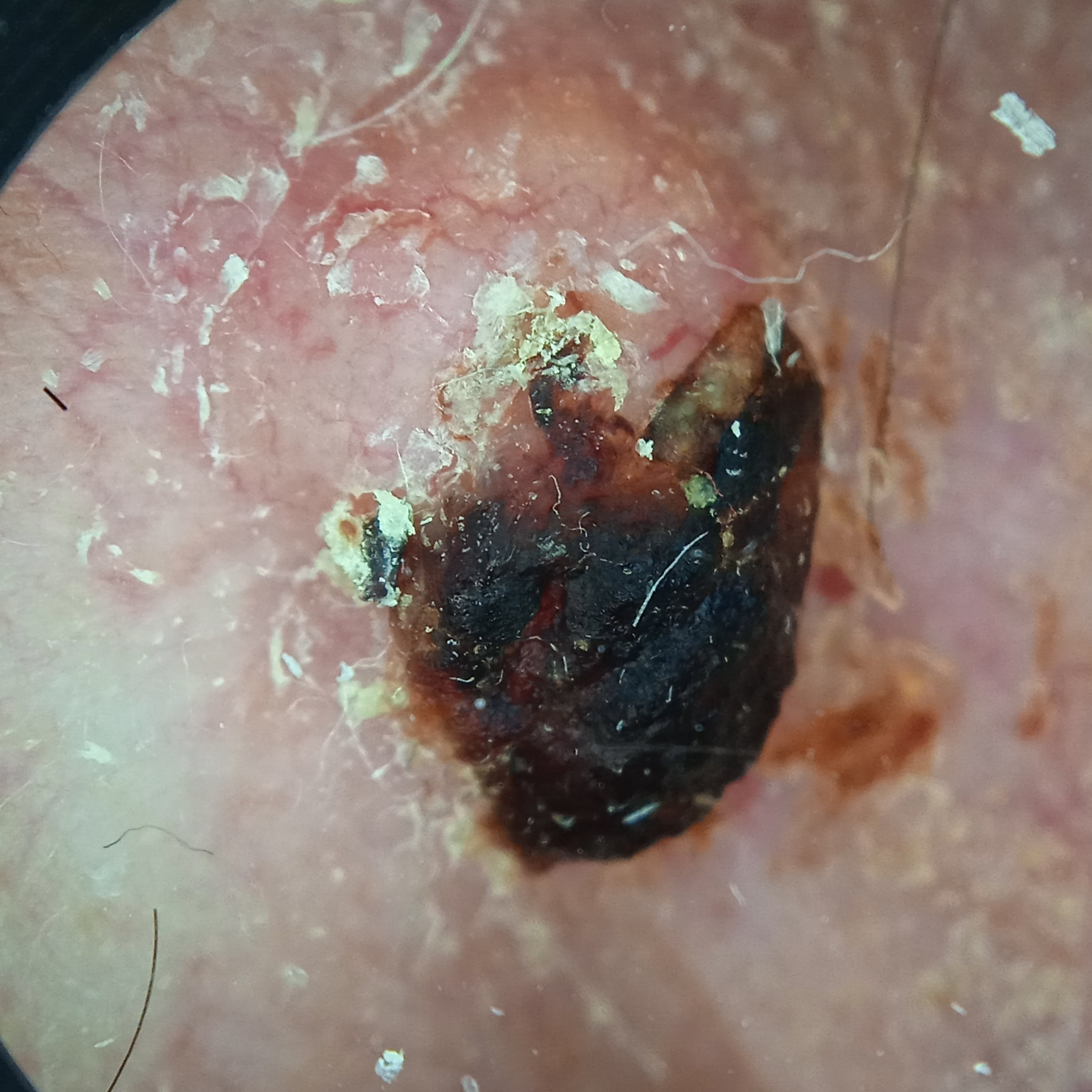subject: male, aged 83 | referral: clinical suspicion of basal cell carcinoma | size: 8 mm | pathology: basal cell carcinoma (biopsy-proven).